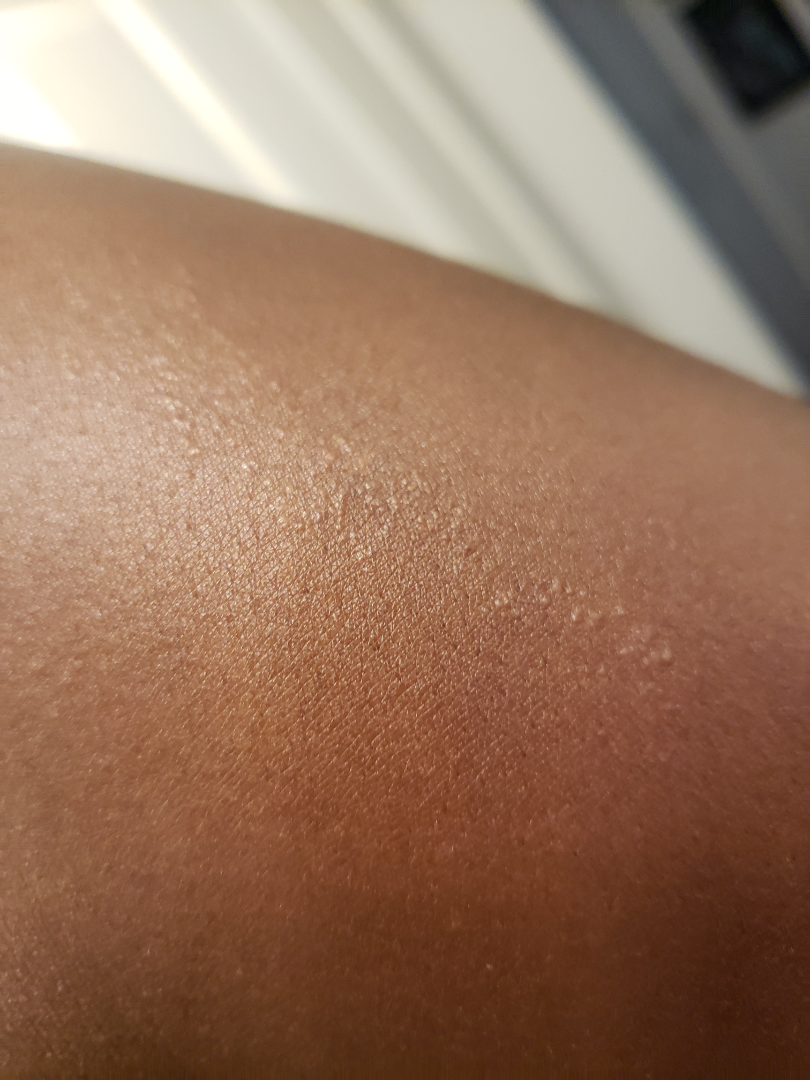Q: What is the differential diagnosis?
A: the differential, in no particular order, includes Eczema and Lichen striatus